Located on the front of the torso; this is a close-up image; skin tone: lay reviewers estimated MST 1–2 — 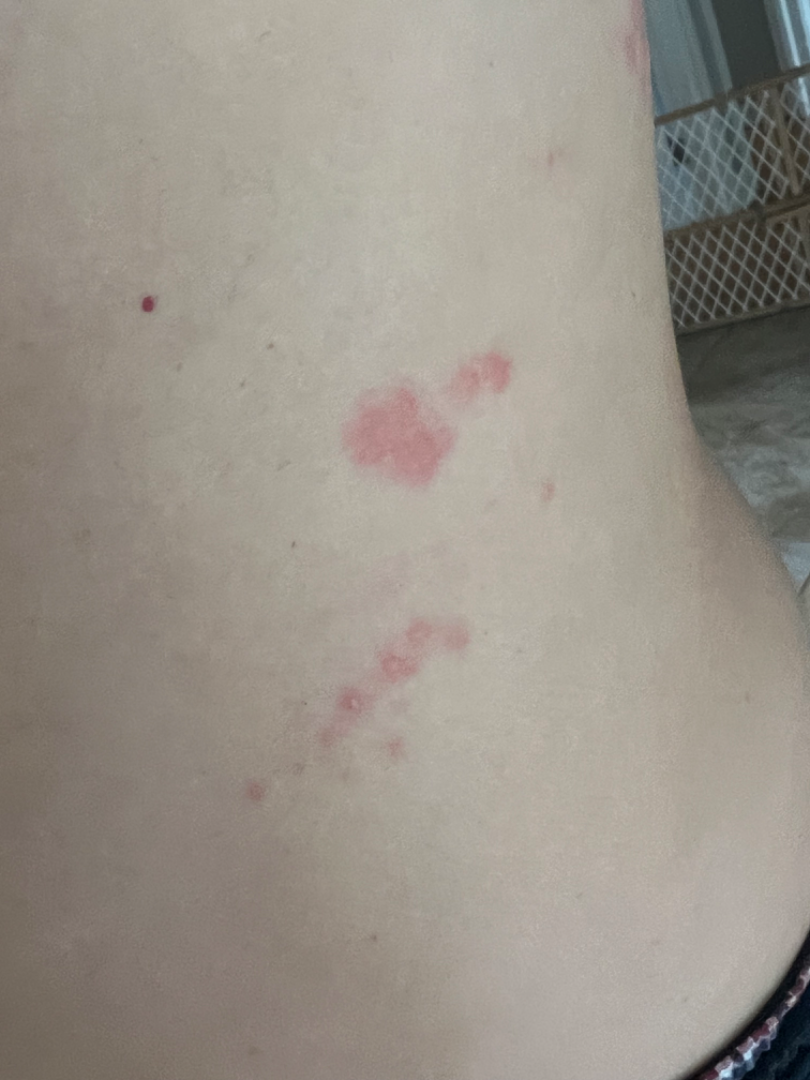The condition could not be reliably identified from the image.